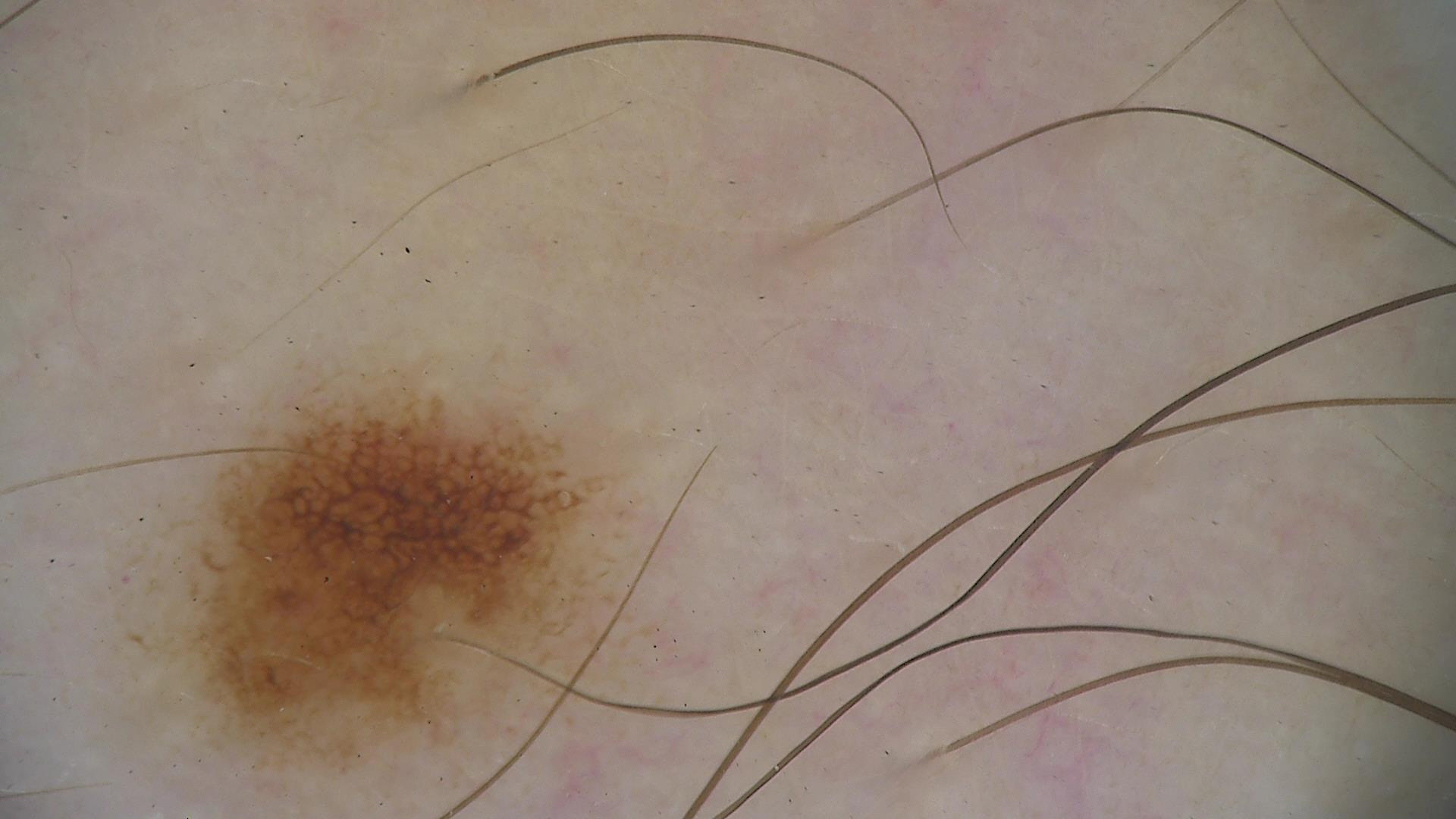Q: What is this lesion?
A: dysplastic junctional nevus (expert consensus)